The subject is 18–29, female; the lesion involves the arm, head or neck, back of the hand and palm; the photograph was taken at an angle.
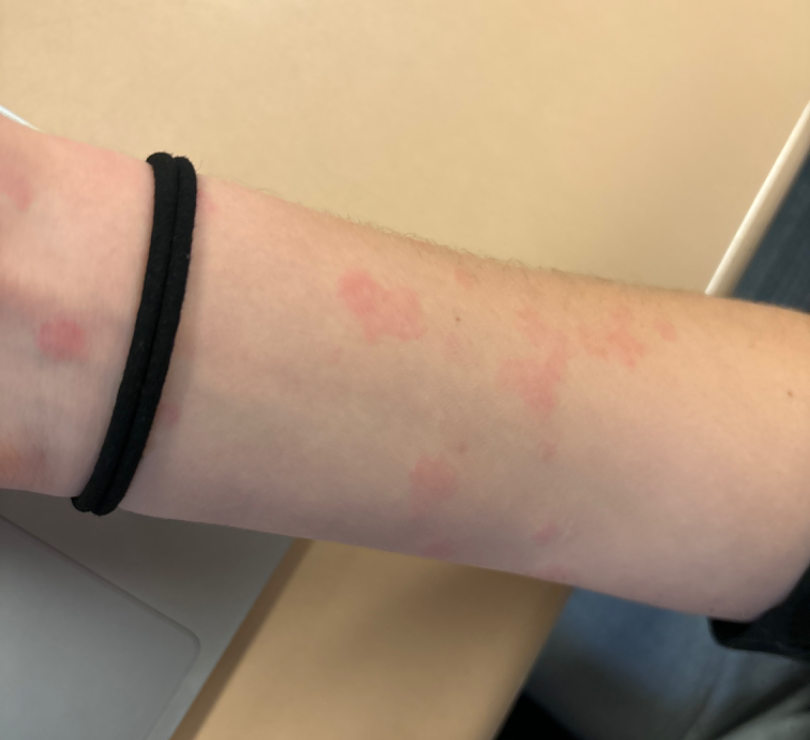patient's own categorization — a rash | patient-reported symptoms — burning, bothersome appearance and darkening | skin tone — FST I; human graders estimated MST 3 | described texture — raised or bumpy | impression — the favored diagnosis is Urticaria; also on the differential is Hypersensitivity.